A dermoscopy image of a single skin lesion: 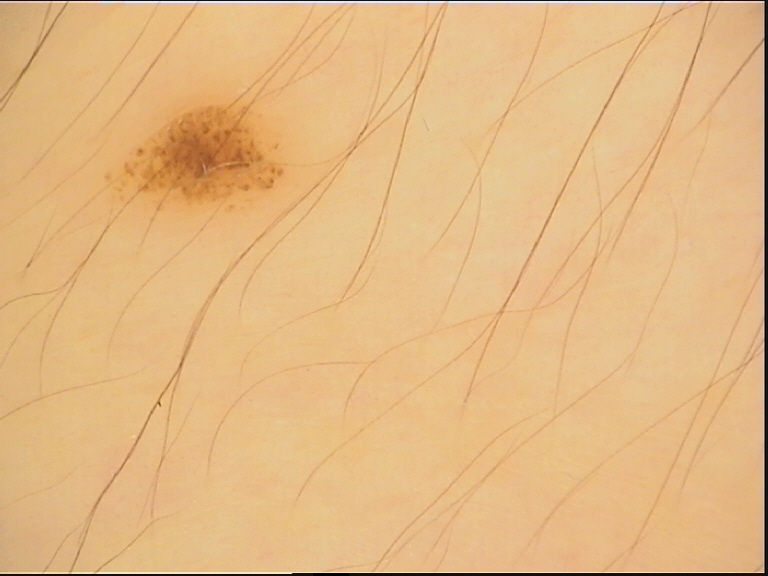The diagnosis was a dysplastic junctional nevus.